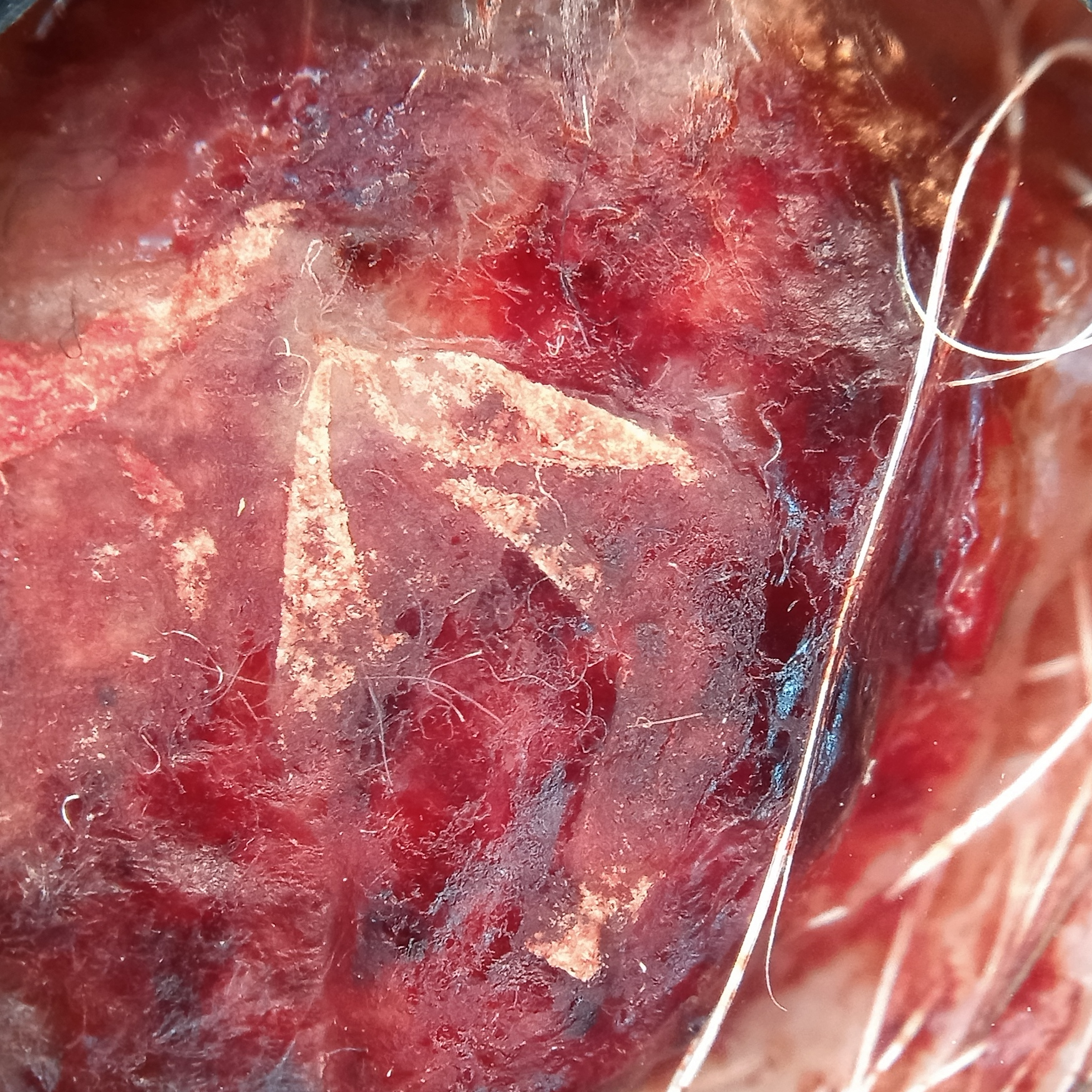The referring clinician suspected melanoma. A skin lesion imaged with a dermatoscope. The patient reports a personal history of cancer. A male subject age 78. The lesion involves the face. Measuring roughly 19.9 mm. Confirmed on histopathology as a melanoma, following excision.